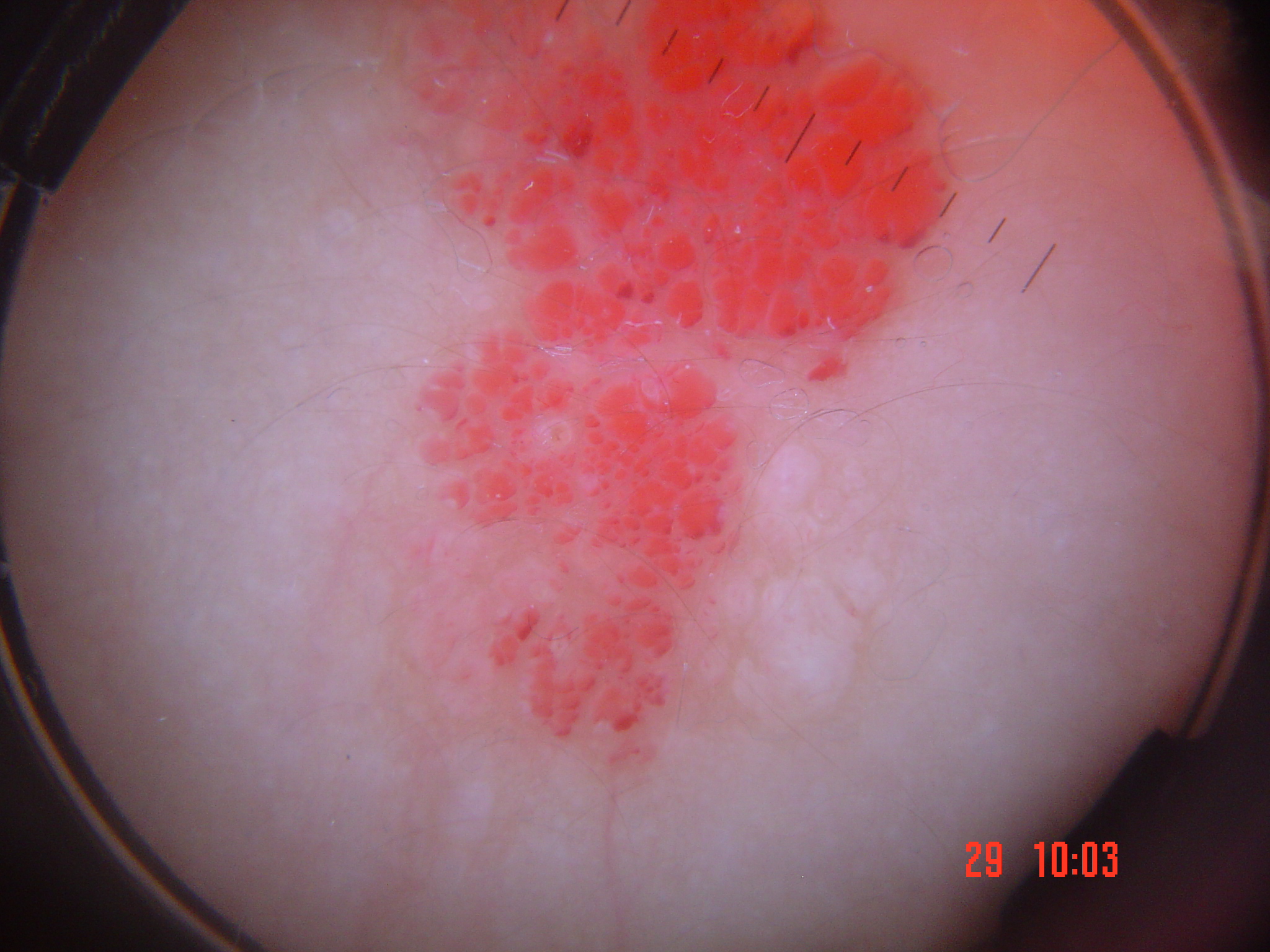{
  "image": "dermatoscopy",
  "diagnosis": {
    "name": "lymphangioma",
    "code": "la",
    "malignancy": "benign",
    "super_class": "non-melanocytic",
    "confirmation": "expert consensus"
  }
}